A dermoscopic view of a skin lesion:
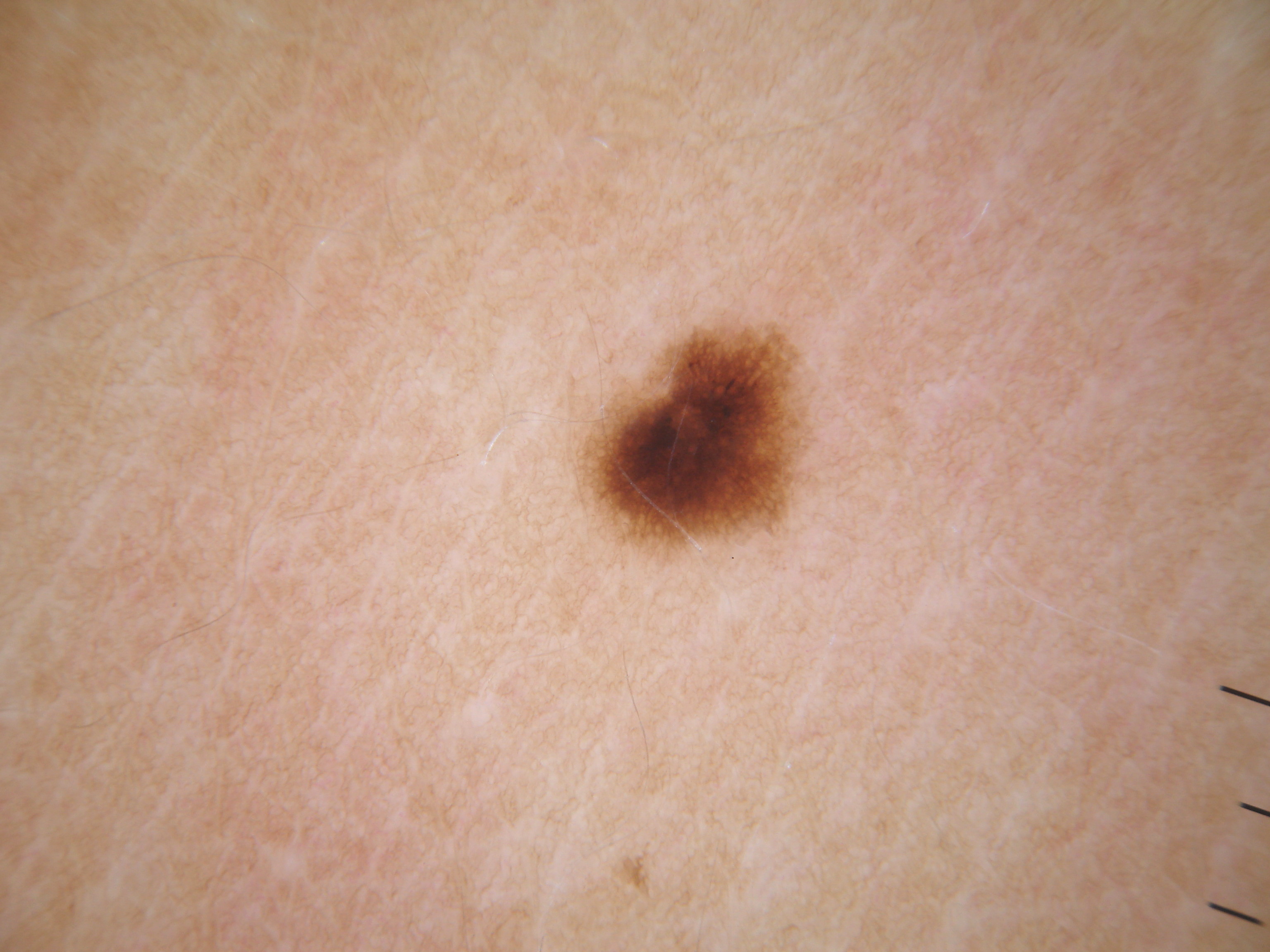In (x1, y1, x2, y2) order, the lesion is bounded by [575, 317, 815, 563].
Dermoscopic review identifies pigment network; no milia-like cysts, globules, streaks, or negative network.
The lesion is small relative to the field of view.
Consistent with a melanocytic nevus.